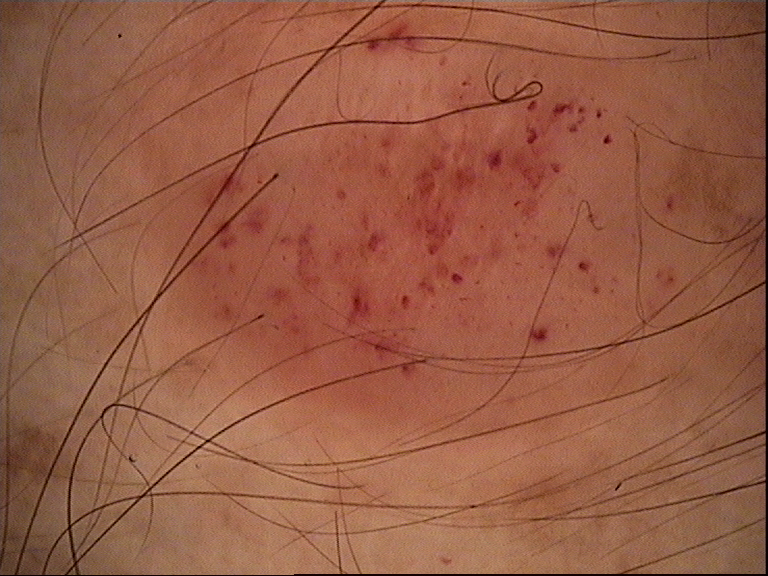Classified as a vascular lesion — a hemangioma.